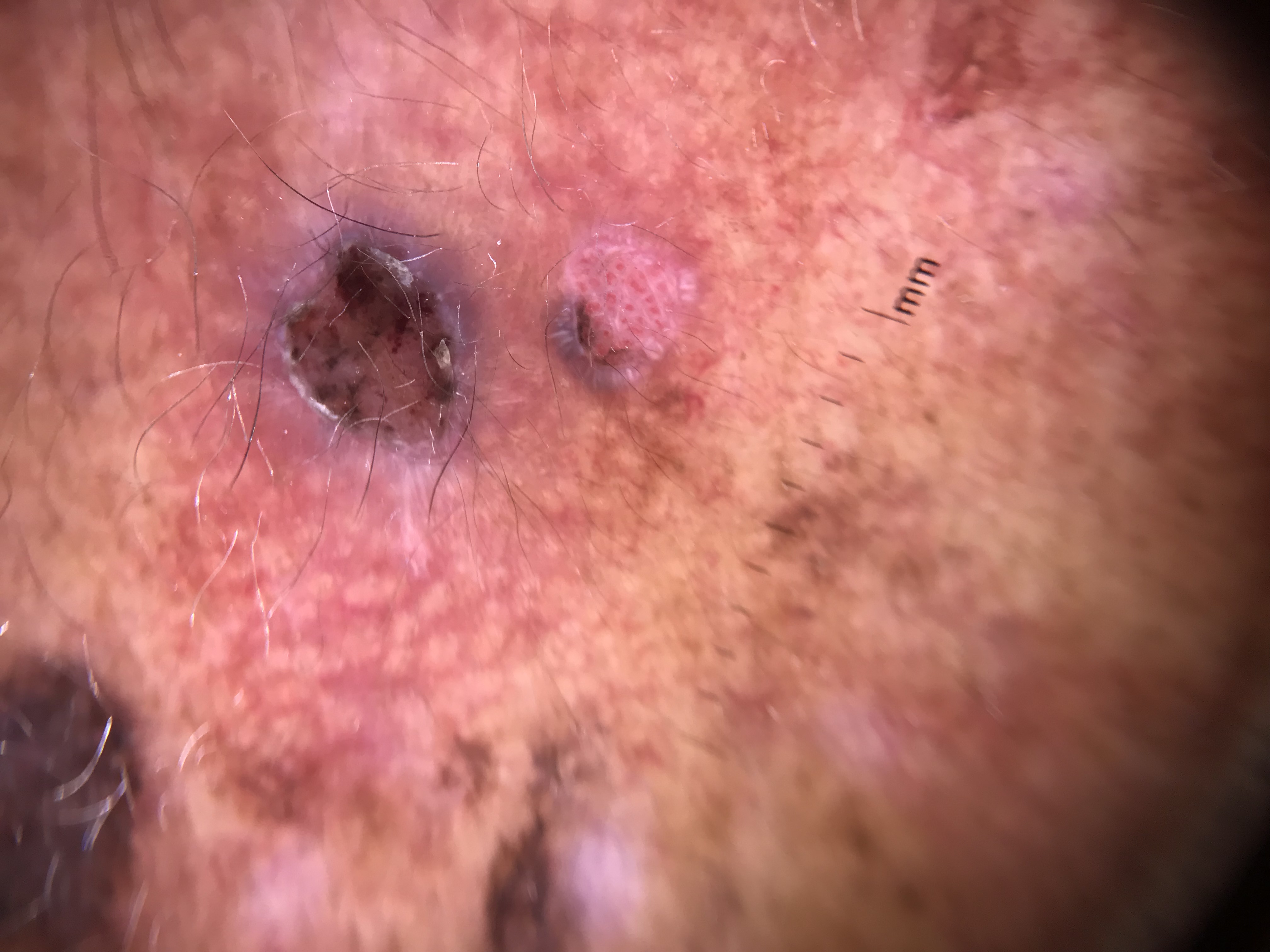modality — dermatoscopy; class — basal cell carcinoma (biopsy-proven).